An image taken at an angle, the contributor is a male aged 18–29, located on the arm:
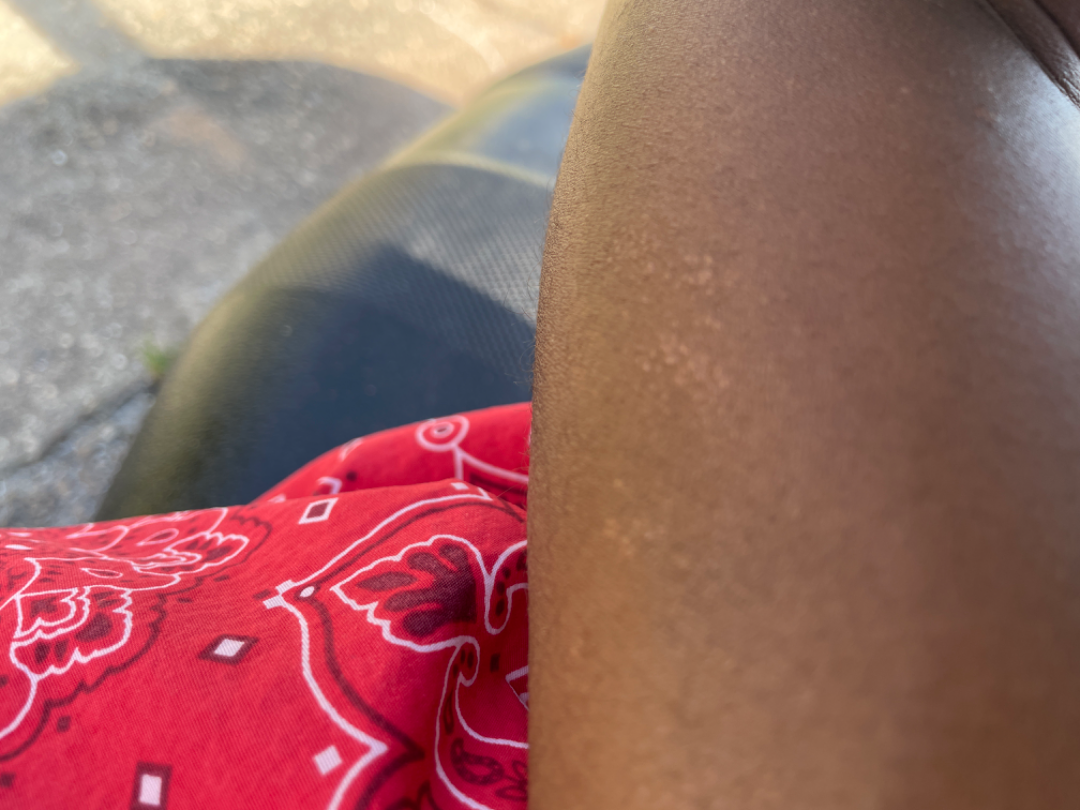Assessment:
No differential diagnosis could be assigned on photographic review.
Clinical context:
Reported duration is one to four weeks. Texture is reported as raised or bumpy. The patient considered this a rash.